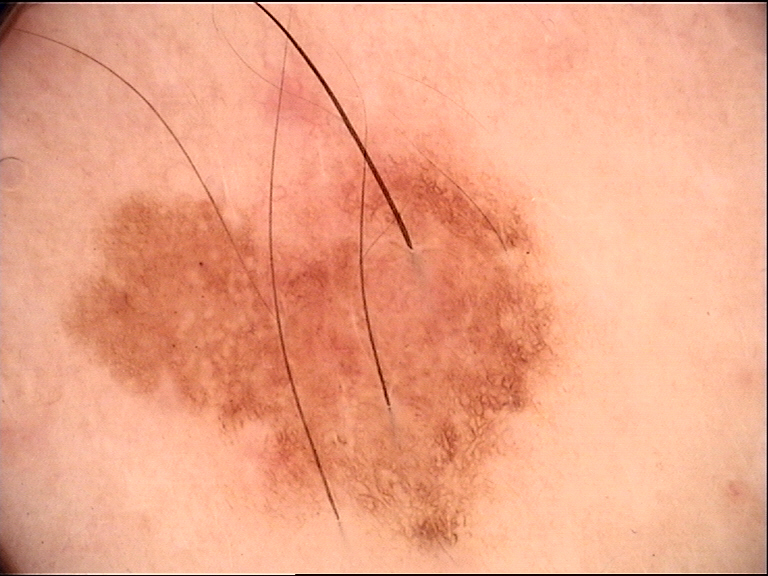<case>
  <image>dermoscopy</image>
  <diagnosis>
    <name>dysplastic junctional nevus</name>
    <code>jd</code>
    <malignancy>benign</malignancy>
    <super_class>melanocytic</super_class>
    <confirmation>expert consensus</confirmation>
  </diagnosis>
</case>